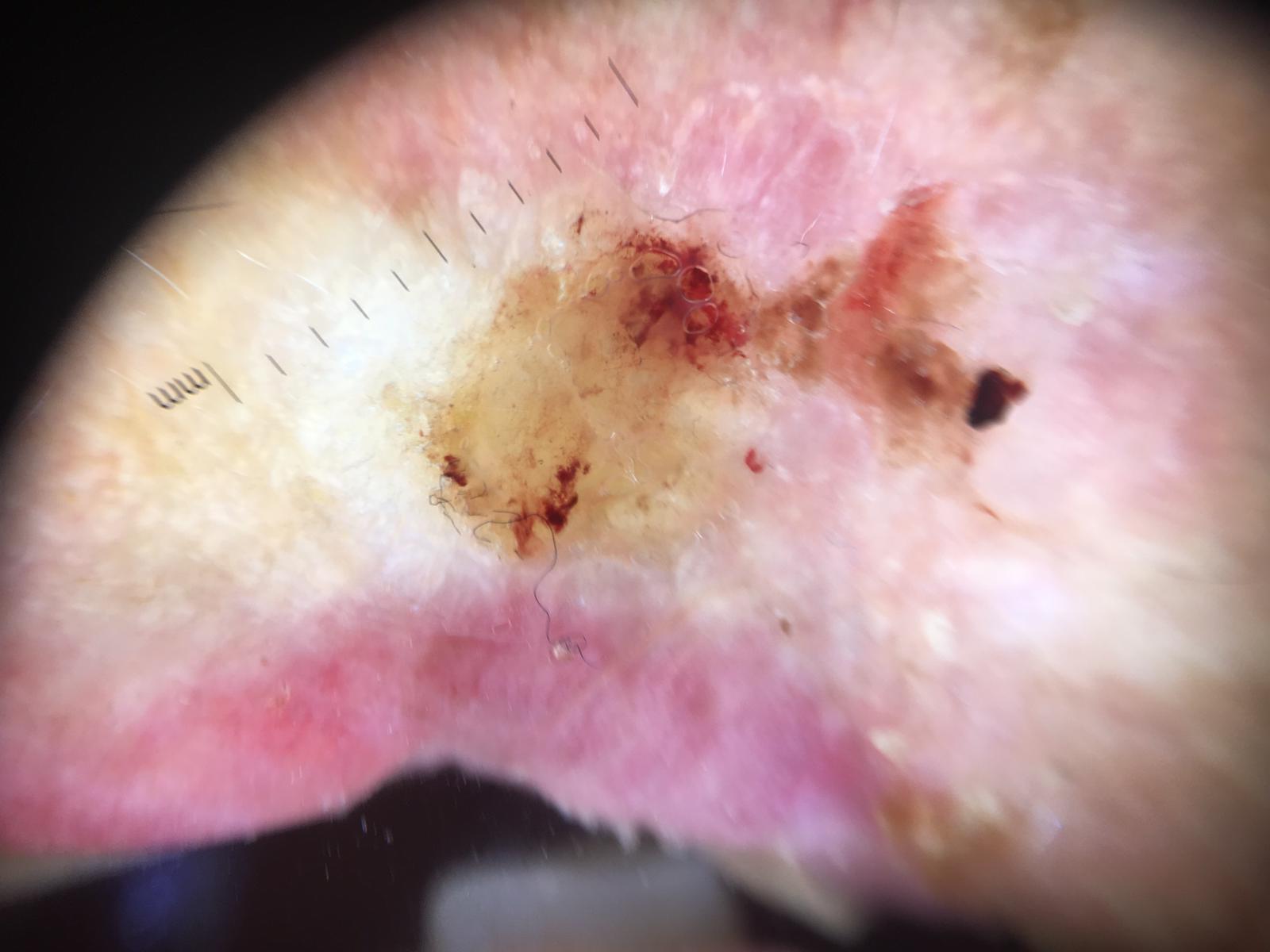Diagnosis: Histopathology confirmed a squamous cell carcinoma.